Dermoscopy of a skin lesion:
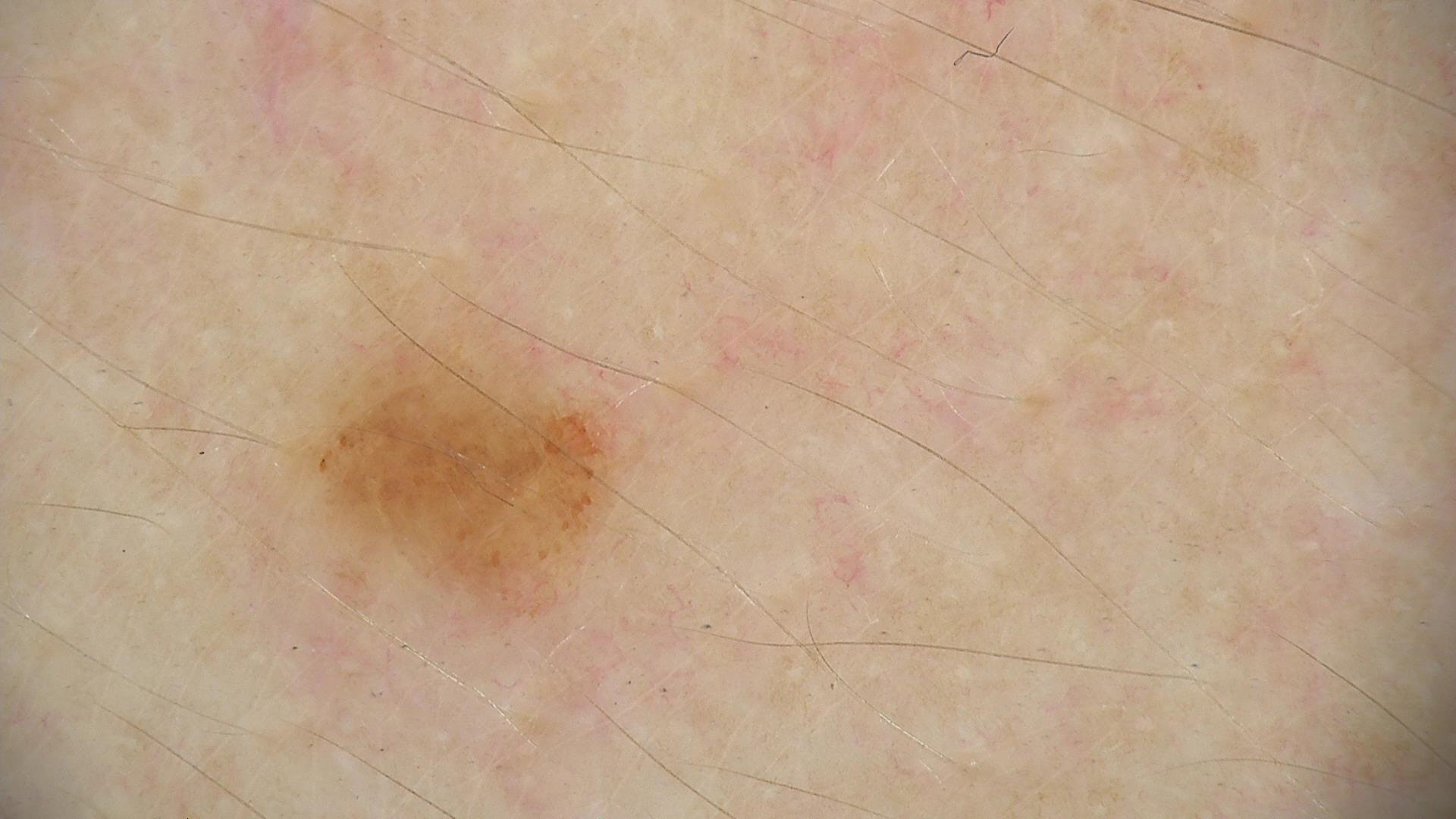Diagnosed as a dysplastic junctional nevus.